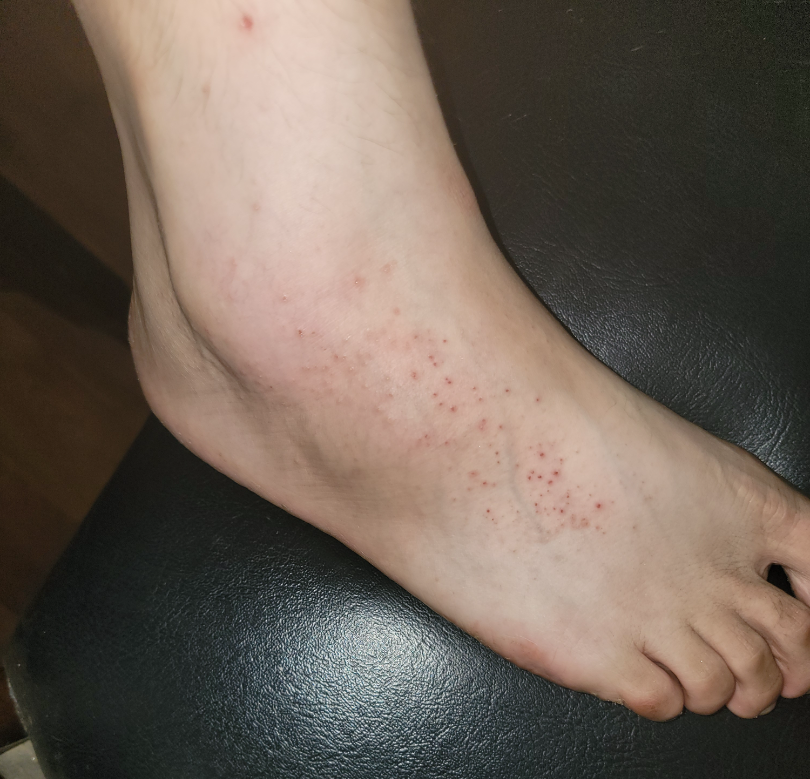Review:
Inflicted skin lesions (weight 0.41); Eczema (weight 0.41); Irritant Contact Dermatitis (weight 0.18).